Symptoms reported: bothersome appearance, enlargement and itching. The contributor reports the condition has been present for about one day. Located on the arm, head or neck and leg. The patient considered this a rash. No constitutional symptoms were reported. The contributor reports the lesion is raised or bumpy. Lay graders estimated Monk Skin Tone 2–3. The patient is 18–29, female. Close-up view: 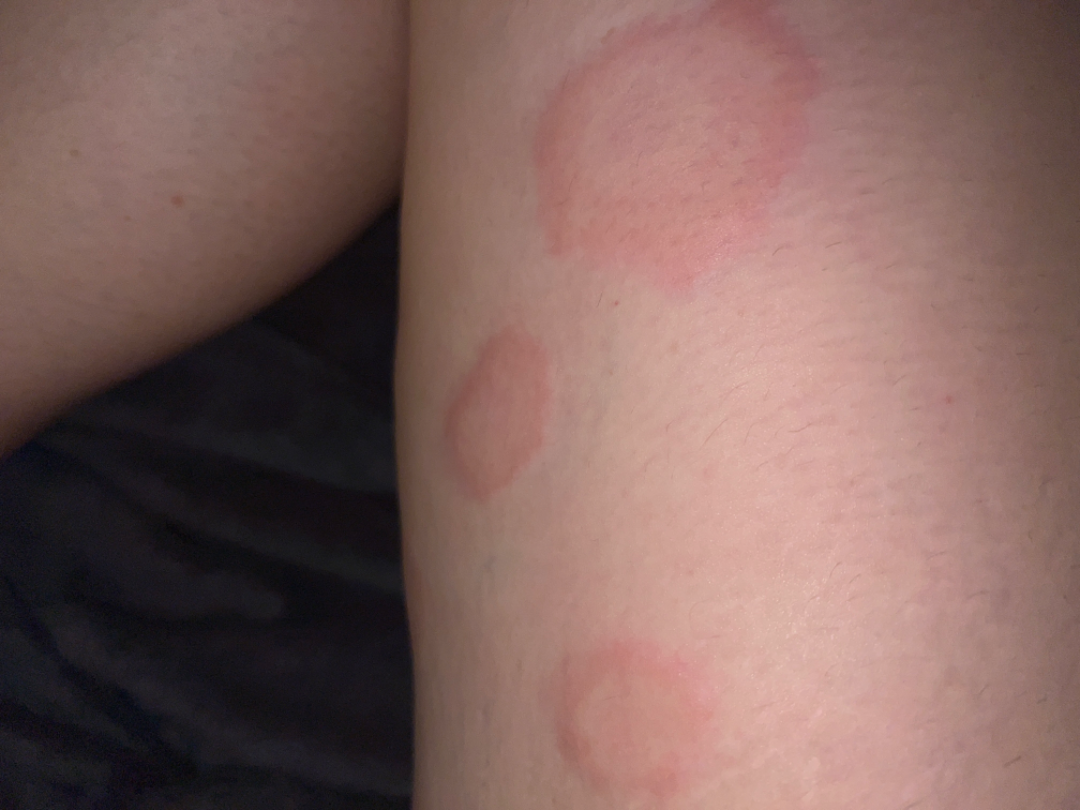Drug Rash (considered); Leukocytoclastic Vasculitis (considered); Erythema multiforme (considered).